The head or neck, leg, back of the hand, back of the torso, top or side of the foot and front of the torso are involved · an image taken at a distance.
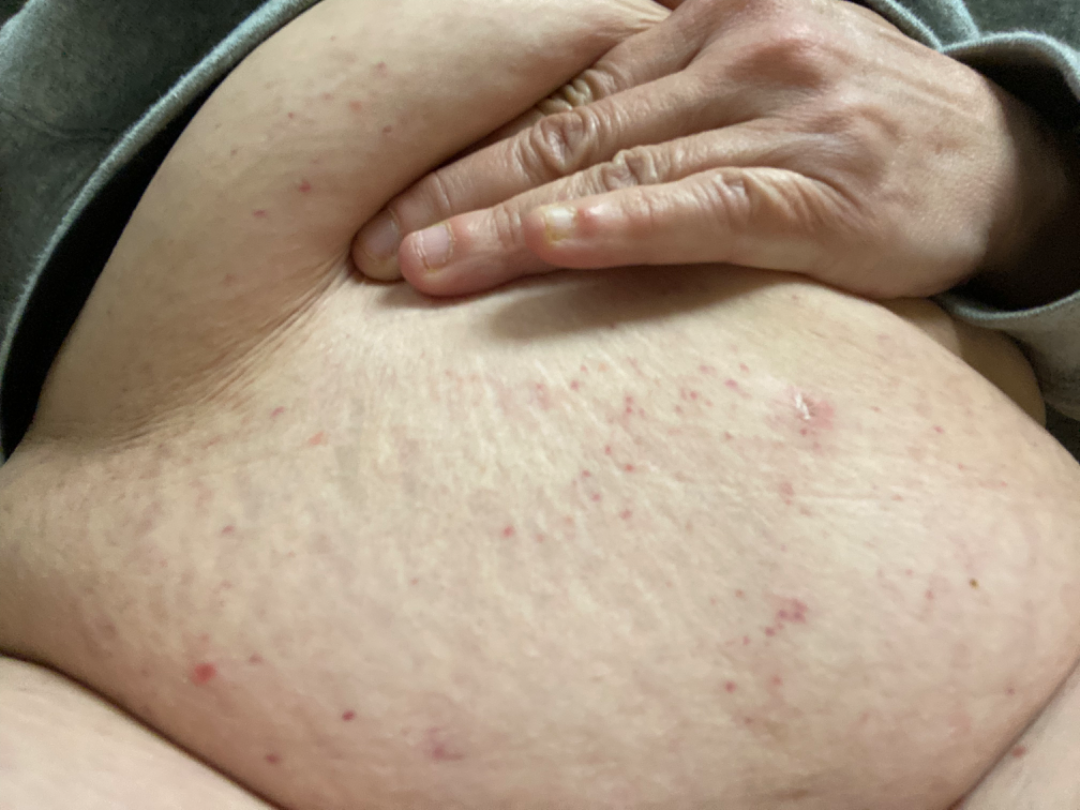Review:
Scabies, Eczema and Hypersensitivity were considered with similar weight.